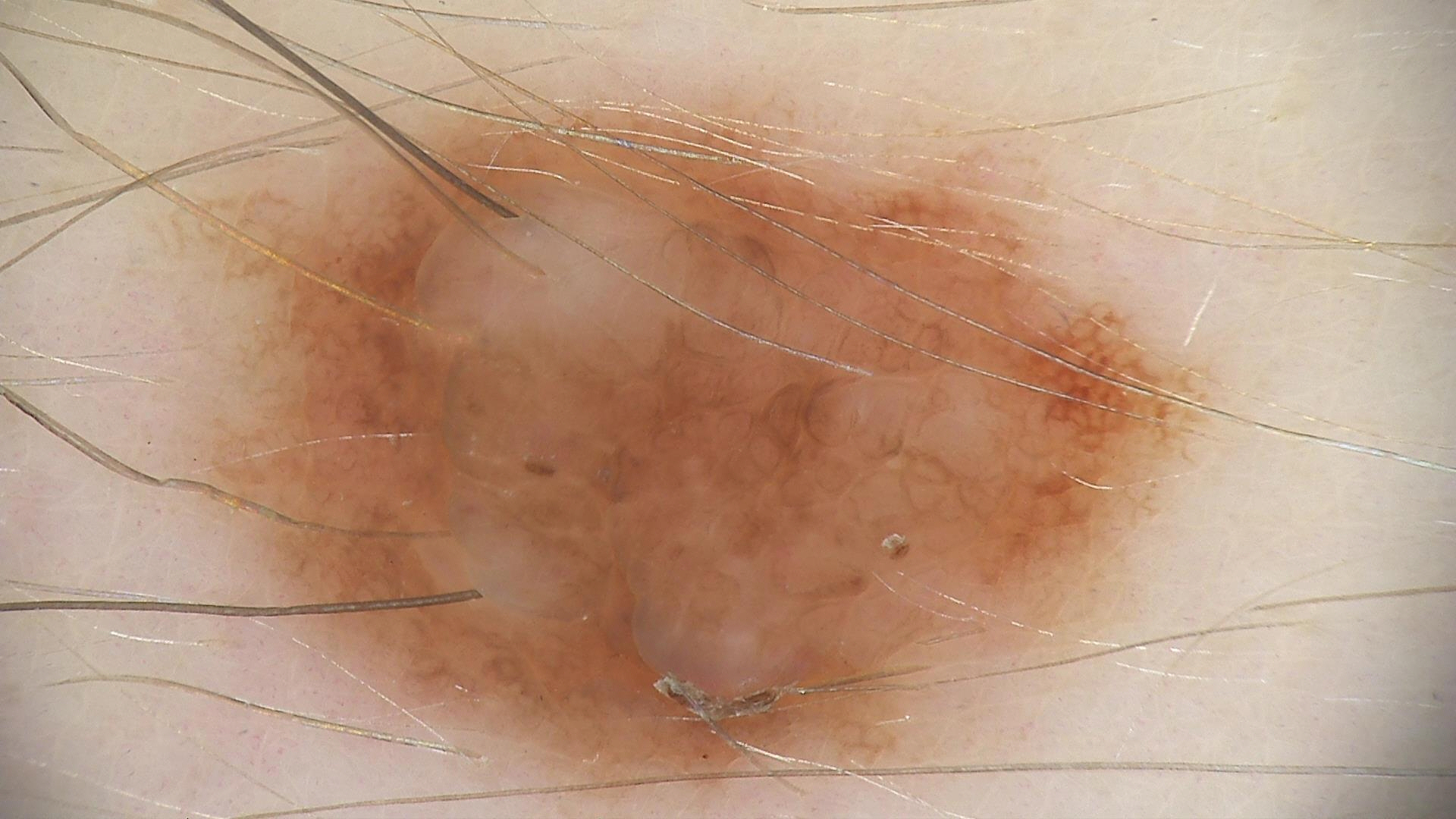A dermatoscopic image of a skin lesion. Diagnosed as a benign lesion — a dysplastic compound nevus.